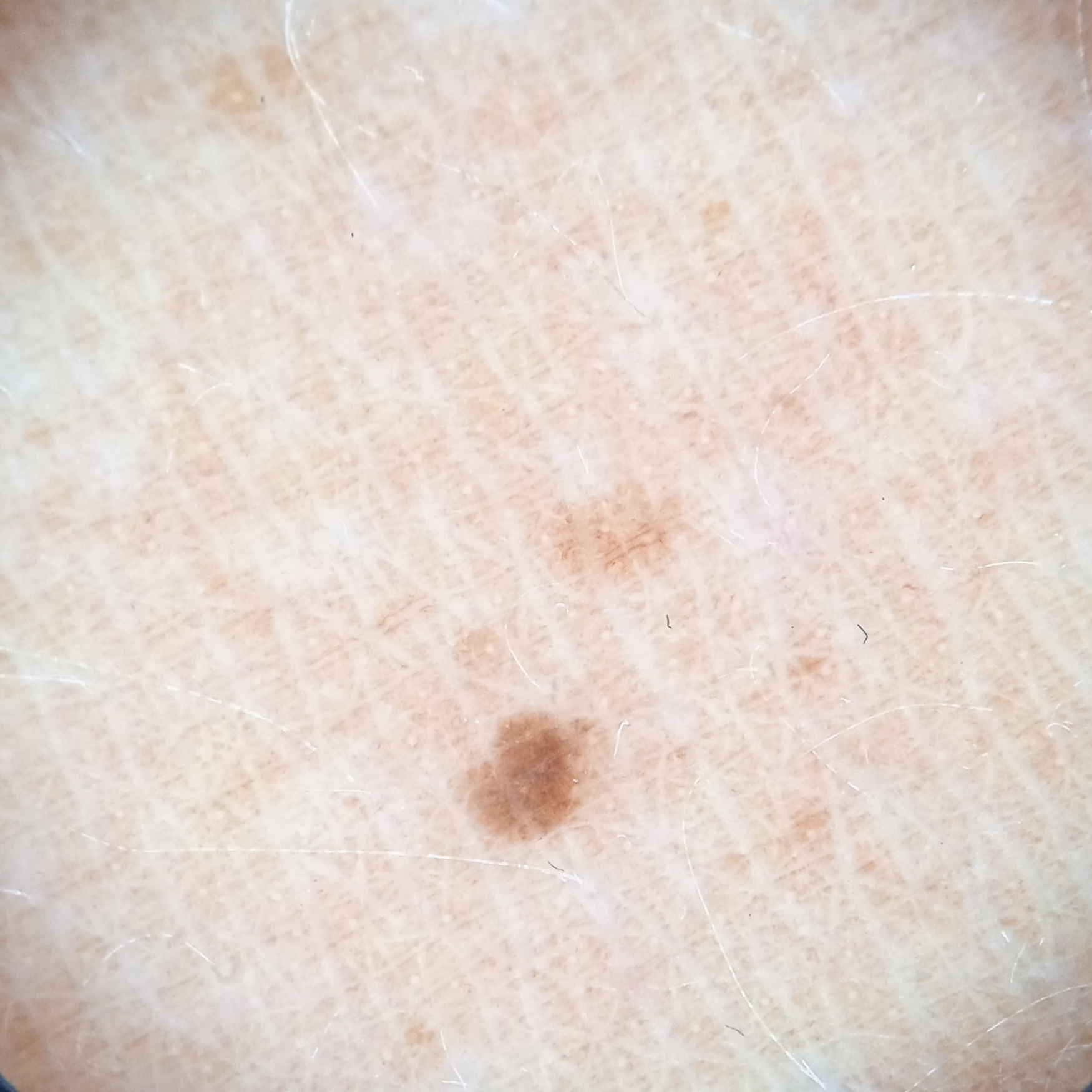Clinical context:
A moderate number of moles by the patient's own estimate. By self-report, a history of sunbed use, no personal history of skin cancer, and no family history of skin cancer. A female subject aged 47. Dermoscopy of a skin lesion. Collected as part of a research study, without a referral diagnosis. The patient says their skin tans without first burning. The lesion is on the back. The lesion measures approximately 1.8 mm.
Assessment:
The diagnostic impression was a melanocytic nevus.